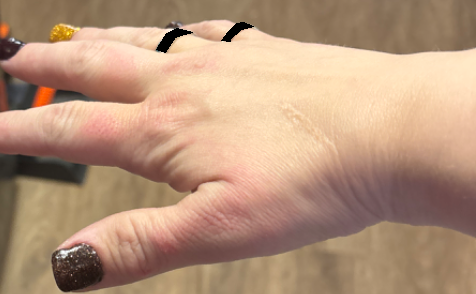The photograph was taken at a distance. On remote dermatologist review, Eczema (primary).